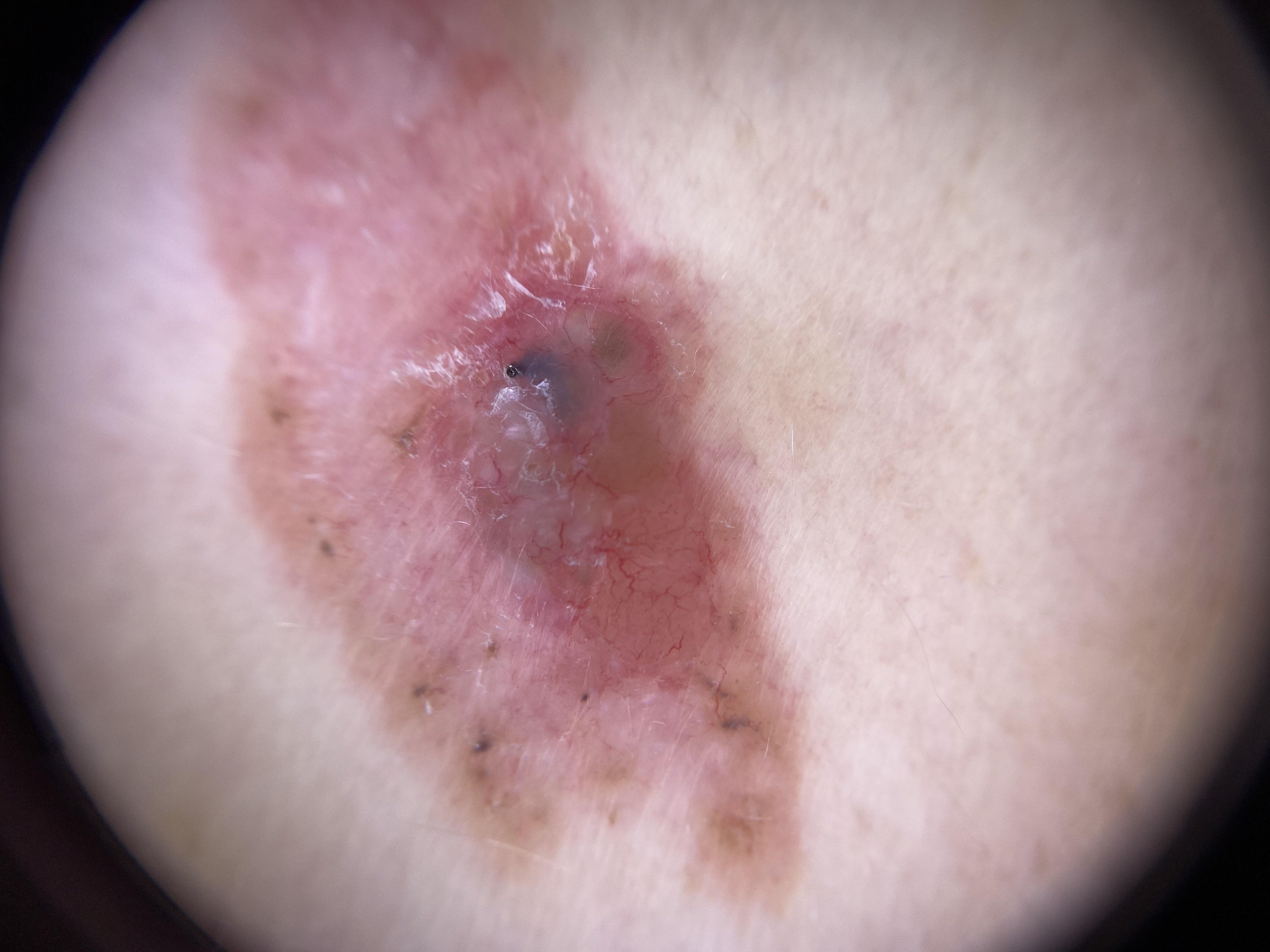A female subject roughly 70 years of age. A contact-polarized dermoscopy image of a skin lesion. The lesion was found on the trunk (the posterior trunk). Histopathologically confirmed as a basal cell carcinoma.